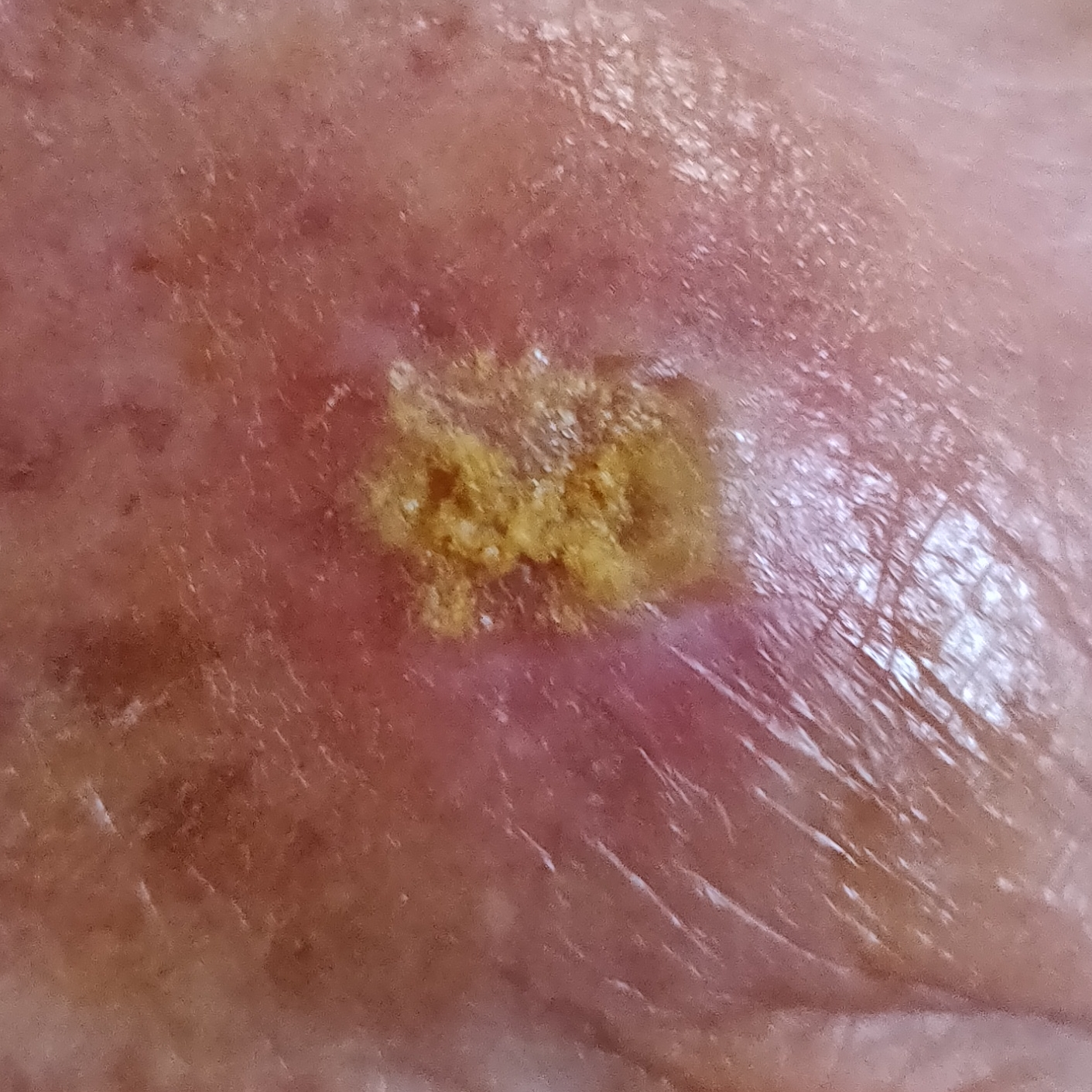Notes:
• skin phototype: II
• subject: male, age 78
• size: 15 × 10 mm
• symptoms: itching, growth, elevation, change in appearance, pain
• diagnosis: actinic keratosis (biopsy-proven)